A skin lesion imaged with a dermatoscope:
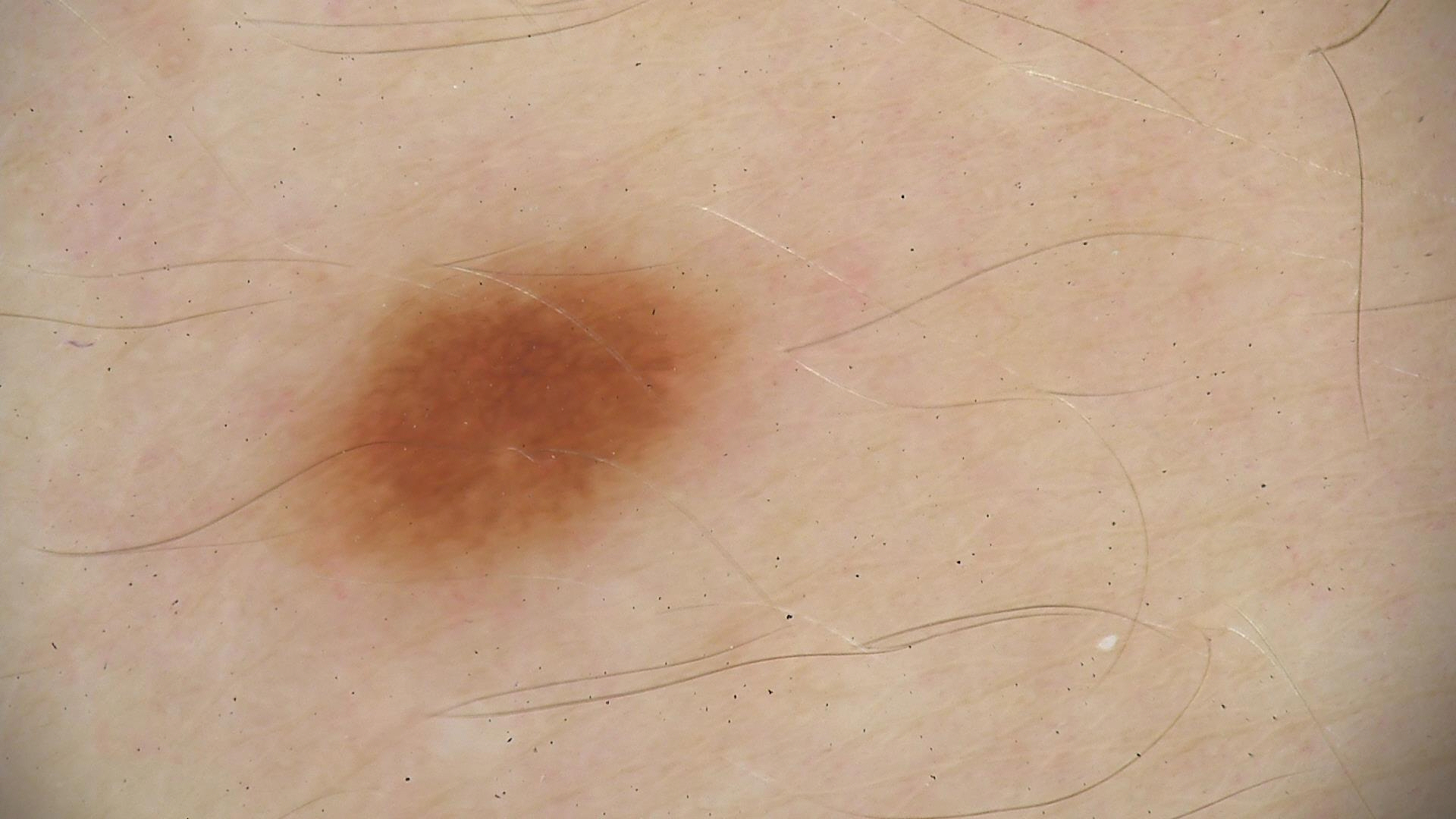Labeled as a dysplastic junctional nevus.